An image taken at a distance:
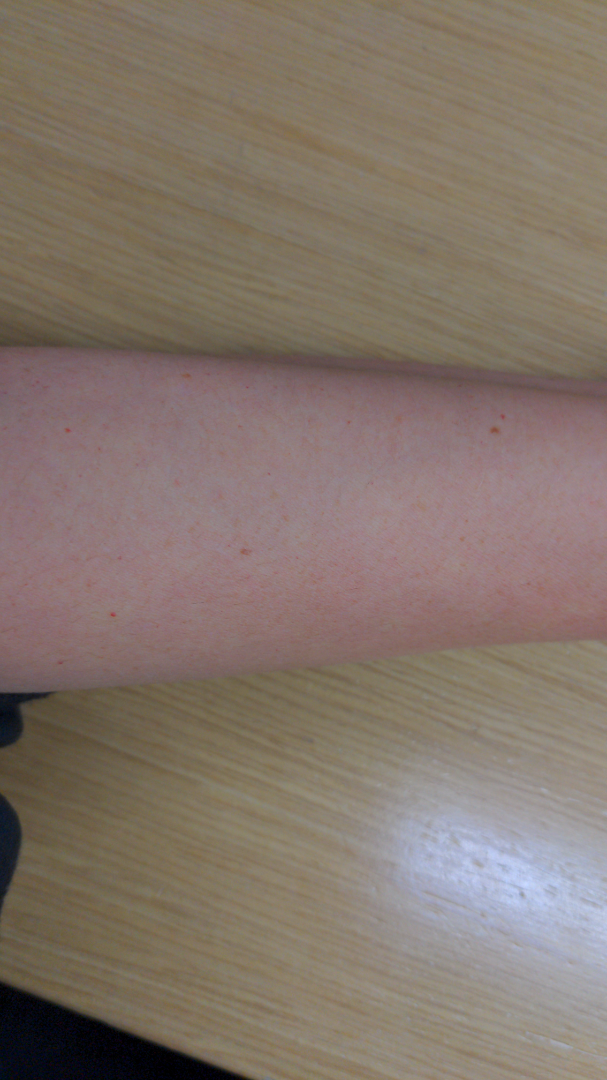impression: Drug Rash and Hypersensitivity were each considered, in no particular order.